The patient considered this a rash; the affected area is the arm; texture is reported as rough or flaky; reported lesion symptoms include itching and burning; the patient is a male aged 18–29; the photo was captured at an angle.
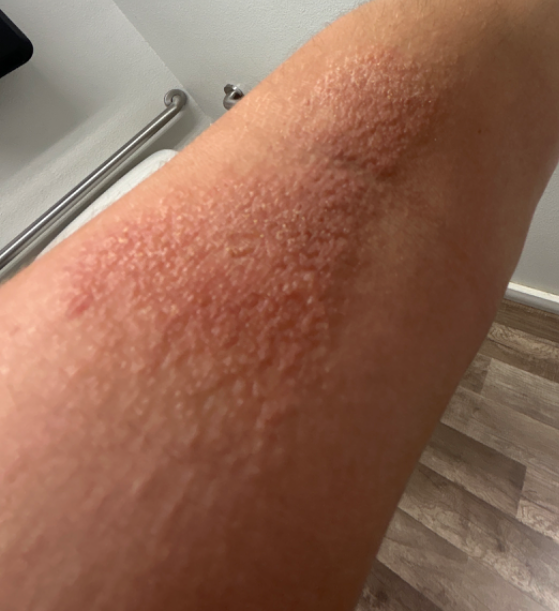{"differential": {"leading": ["Lichen Simplex Chronicus"], "considered": ["Psoriasis"]}}